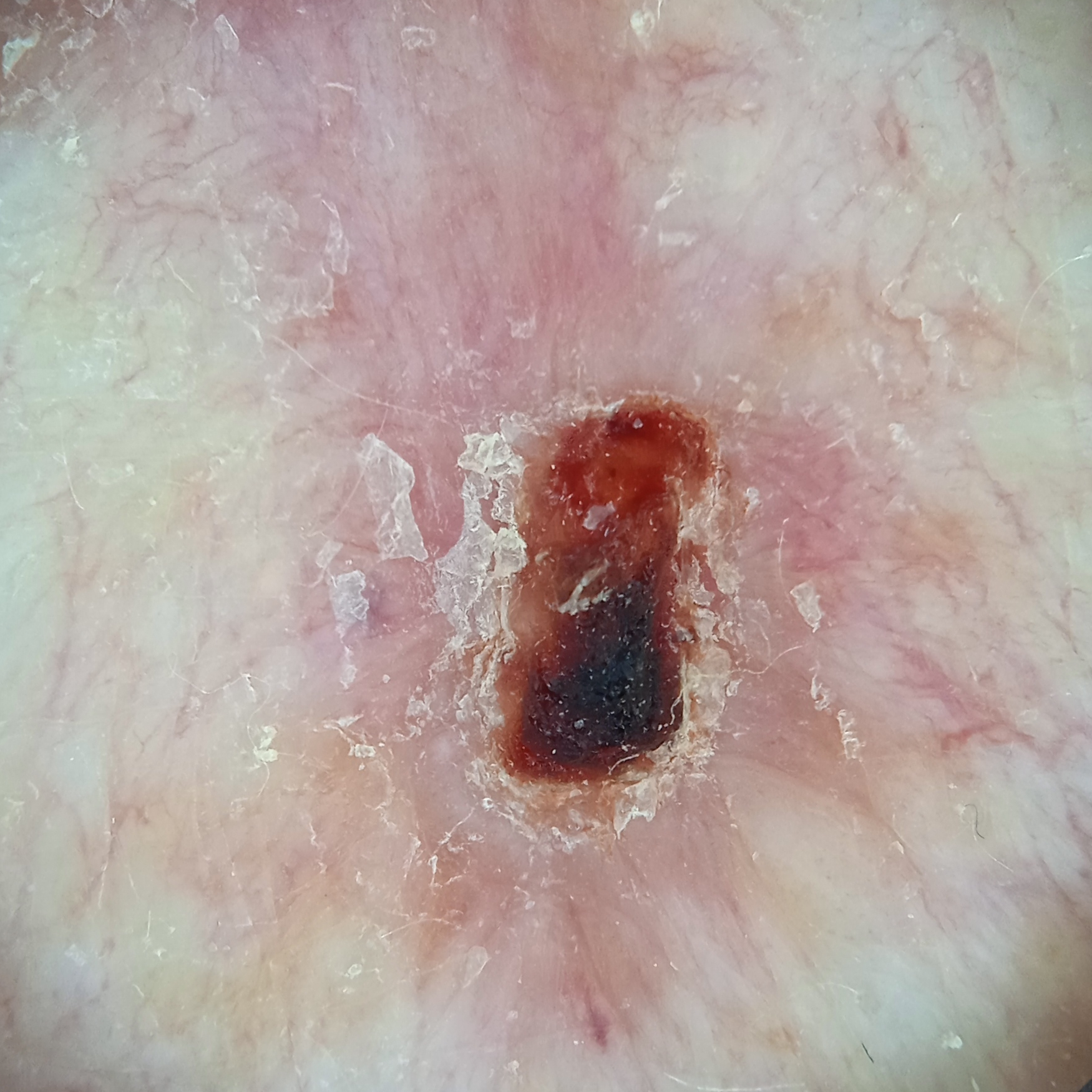Imaged for a research study, with no referral diagnosis recorded. The lesion is on the back. The lesion measures approximately 9.5 mm. The diagnostic impression was a basal cell carcinoma.